Dermoscopy of a skin lesion: 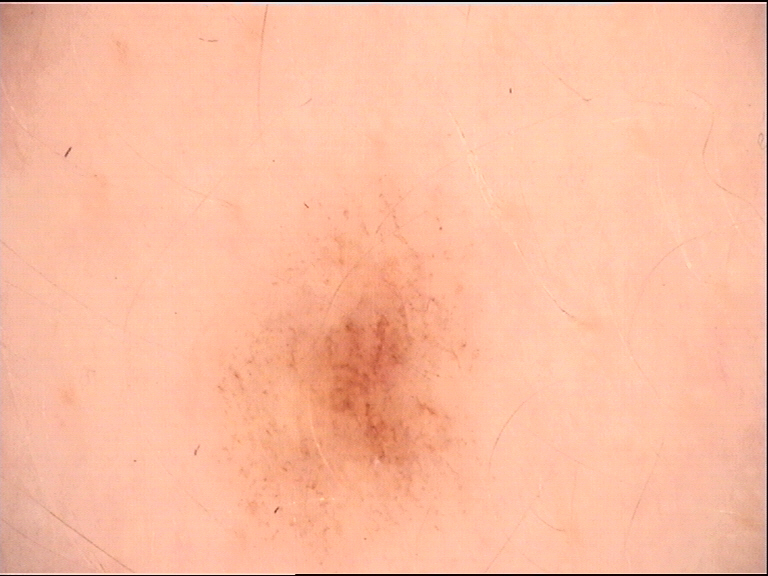The diagnosis was a benign lesion — a dysplastic junctional nevus.